This image was taken at a distance.
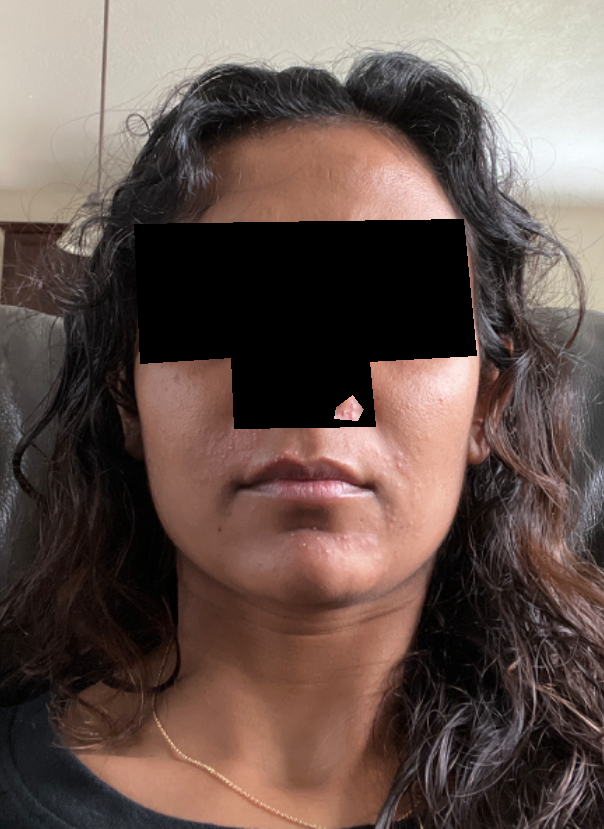{"differential": {"tied_lead": ["Acne", "Milia", "Perioral Dermatitis"]}}